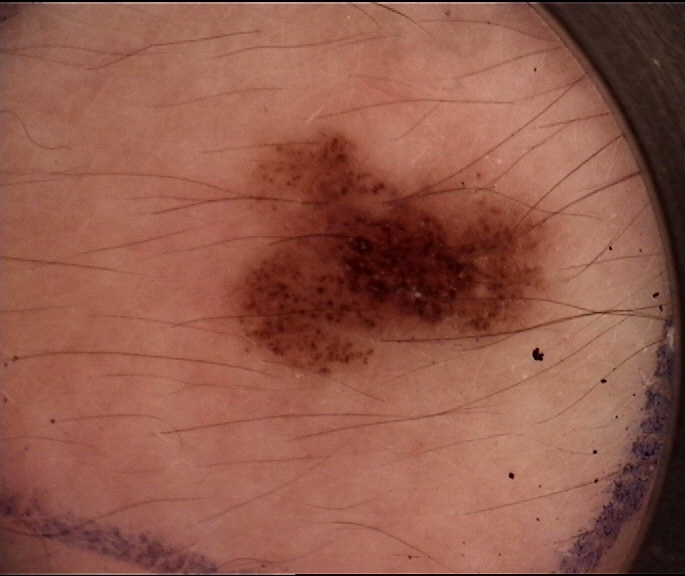Labeled as a dysplastic compound nevus.